Self-categorized by the patient as a rash, texture is reported as rough or flaky and raised or bumpy, this image was taken at a distance, the subject is male, the contributor reports the condition has been present for less than one week, located on the leg:
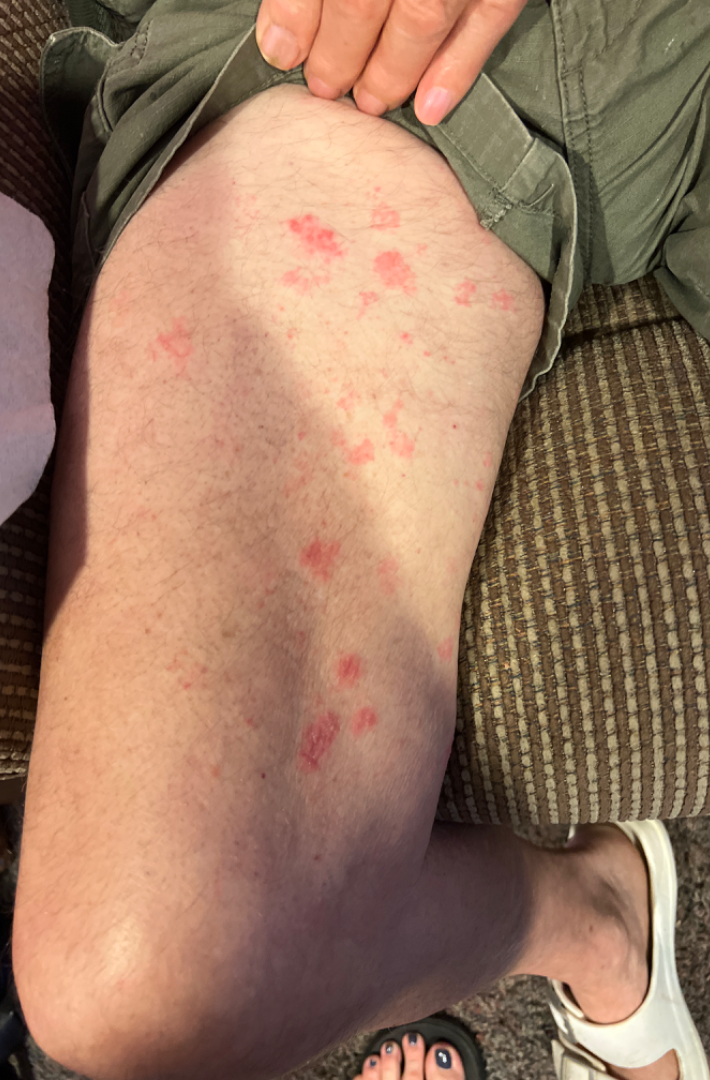Notes:
• assessment · ungradable on photographic review